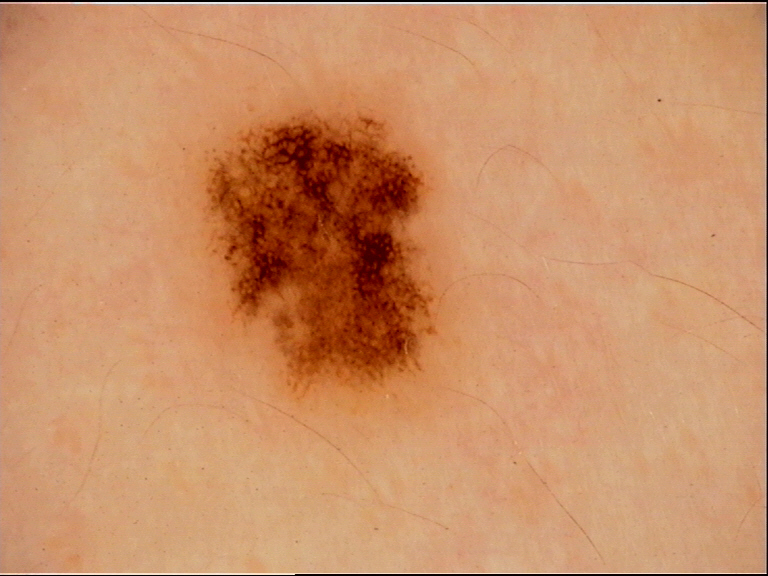Impression:
Diagnosed as a benign lesion — a dysplastic junctional nevus.